A female subject aged 32. A clinical photograph of a skin lesion.
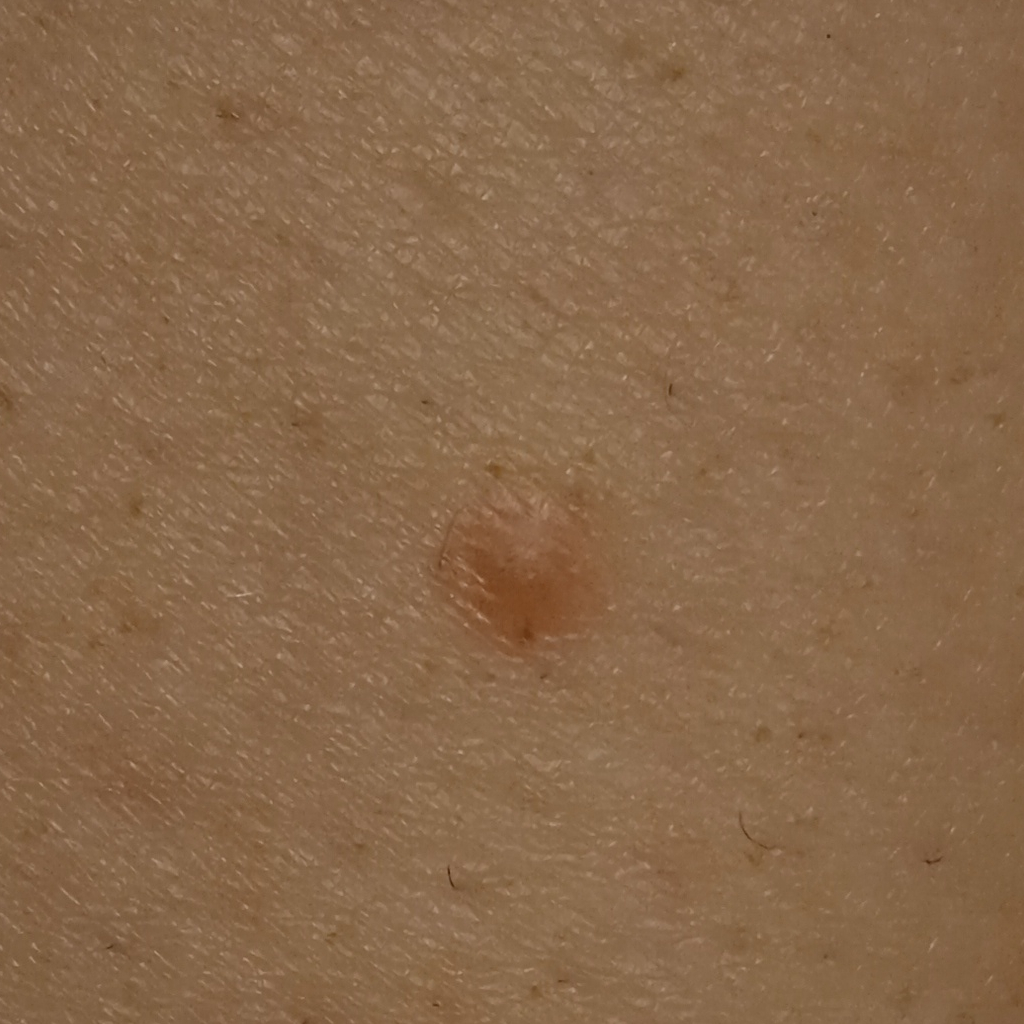Findings:
– size · 5.4 mm
– diagnosis · dermatofibroma (dermatologist consensus)